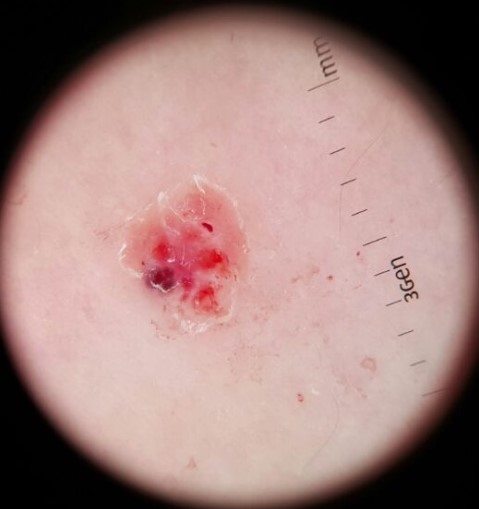Q: What was the diagnostic impression?
A: angiokeratoma (expert consensus)